An image taken at an angle; the leg and arm are involved — 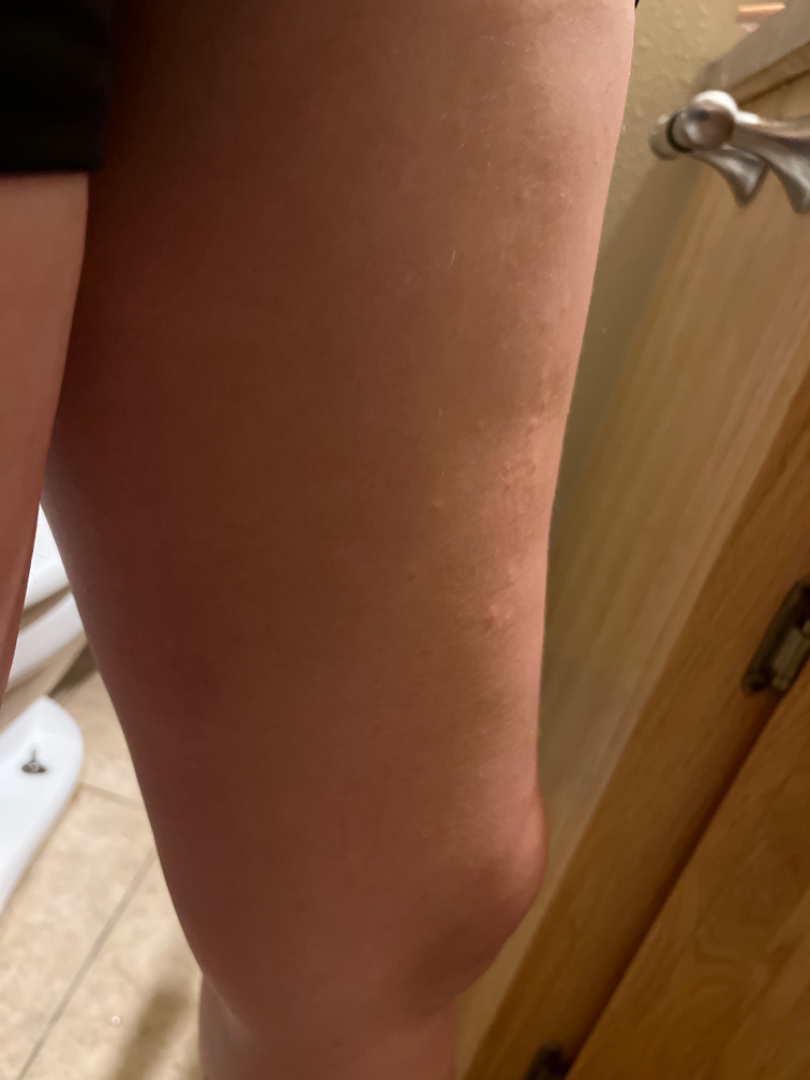The reviewing dermatologist was unable to assign a differential diagnosis from the image.